Located on the leg, front of the torso, back of the torso and arm · no constitutional symptoms were reported · the contributor is 18–29, female · skin tone: Fitzpatrick phototype III; non-clinician graders estimated a MST of 3 · the contributor reports the condition has been present for one to four weeks · the photograph is a close-up of the affected area — 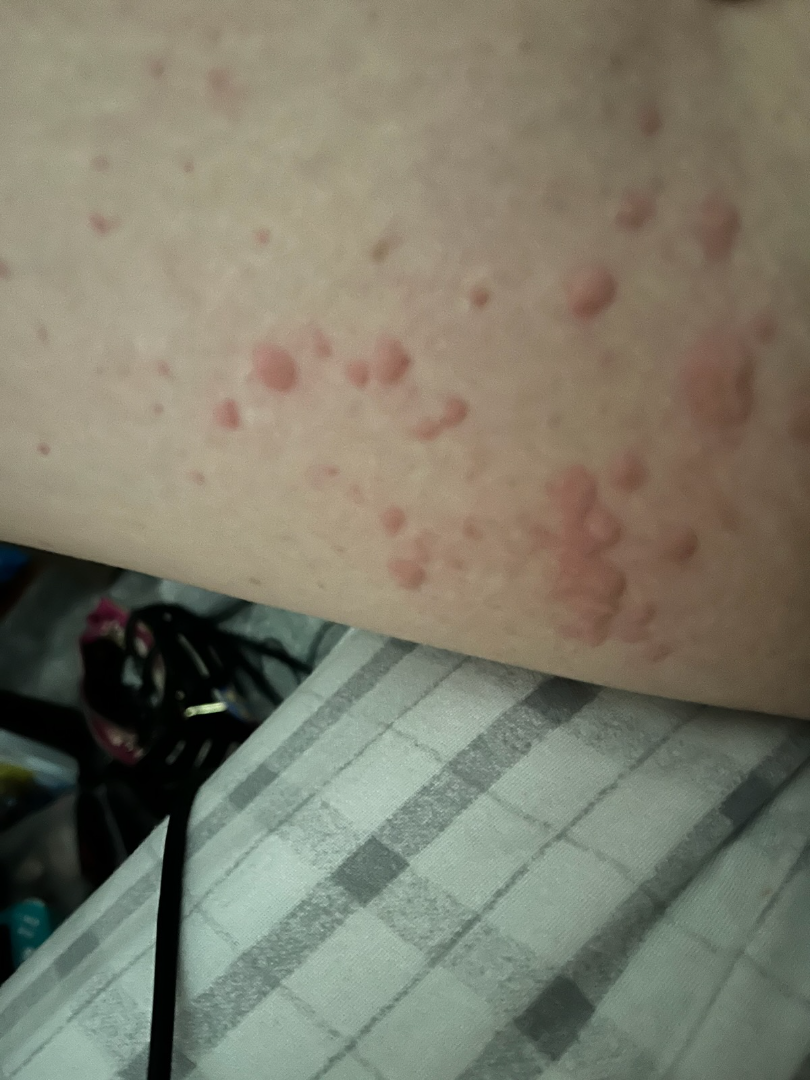Case summary:
– diagnostic considerations: the impression on review was Urticaria